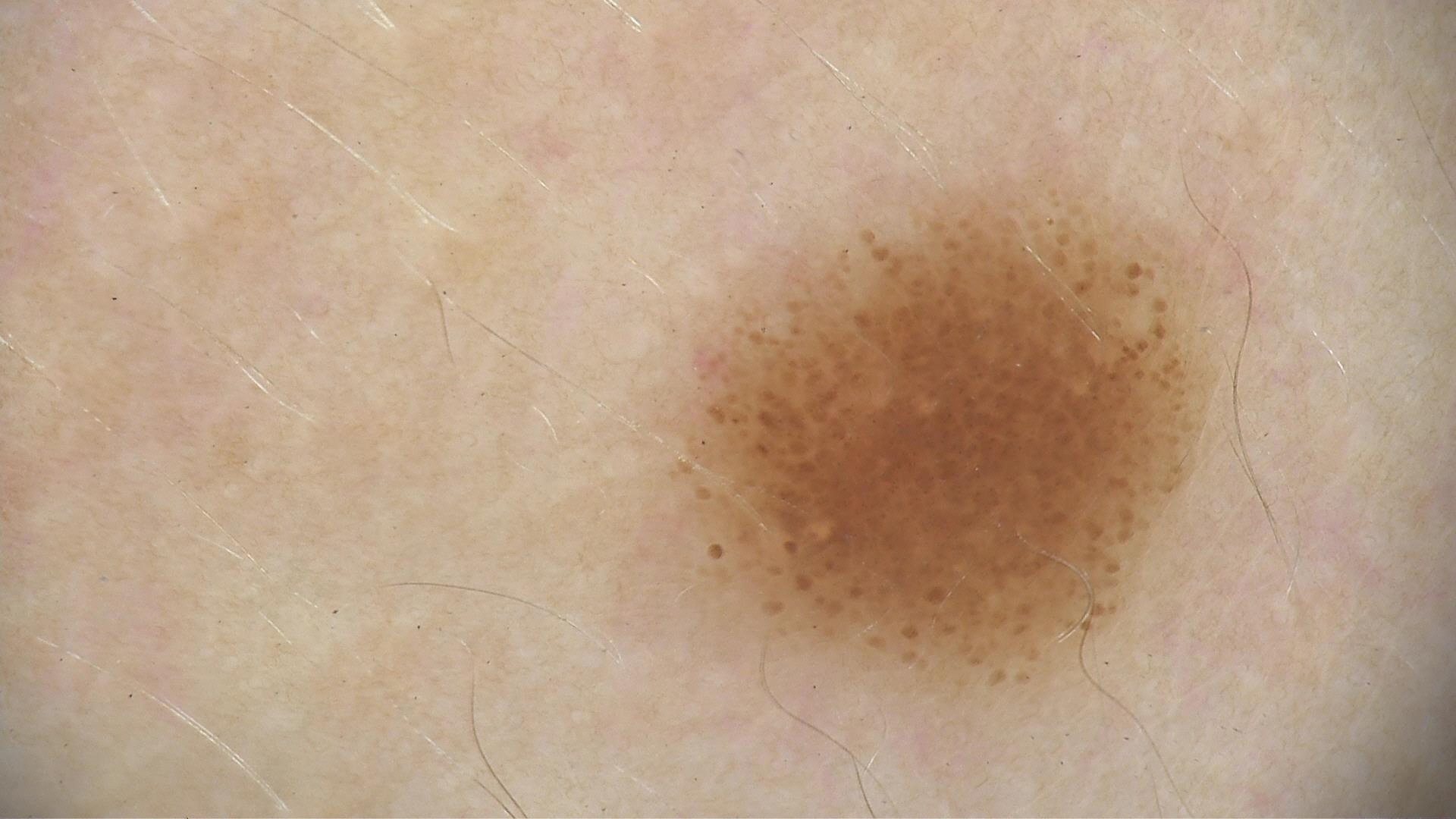A dermoscopy image of a single skin lesion.
Labeled as a benign lesion — a dysplastic junctional nevus.